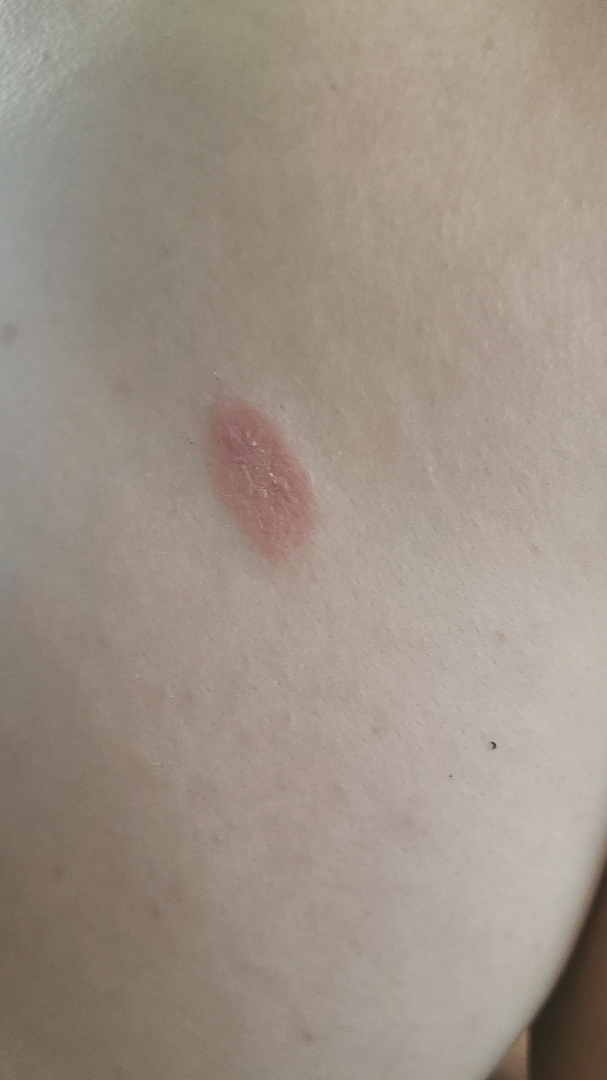Notes:
– lesion texture · rough or flaky
– duration · one to four weeks
– self-categorized as · skin that appeared healthy to them
– symptoms · bothersome appearance
– view · close-up
– other reported symptoms · none reported
– location · back of the torso
– clinical impression · favoring Pityriasis rosea; possibly Eczema; a remote consideration is Psoriasis